The contributor is a female aged 18–29. An image taken at a distance. Reported duration is less than one week. Texture is reported as raised or bumpy. Located on the front of the torso:
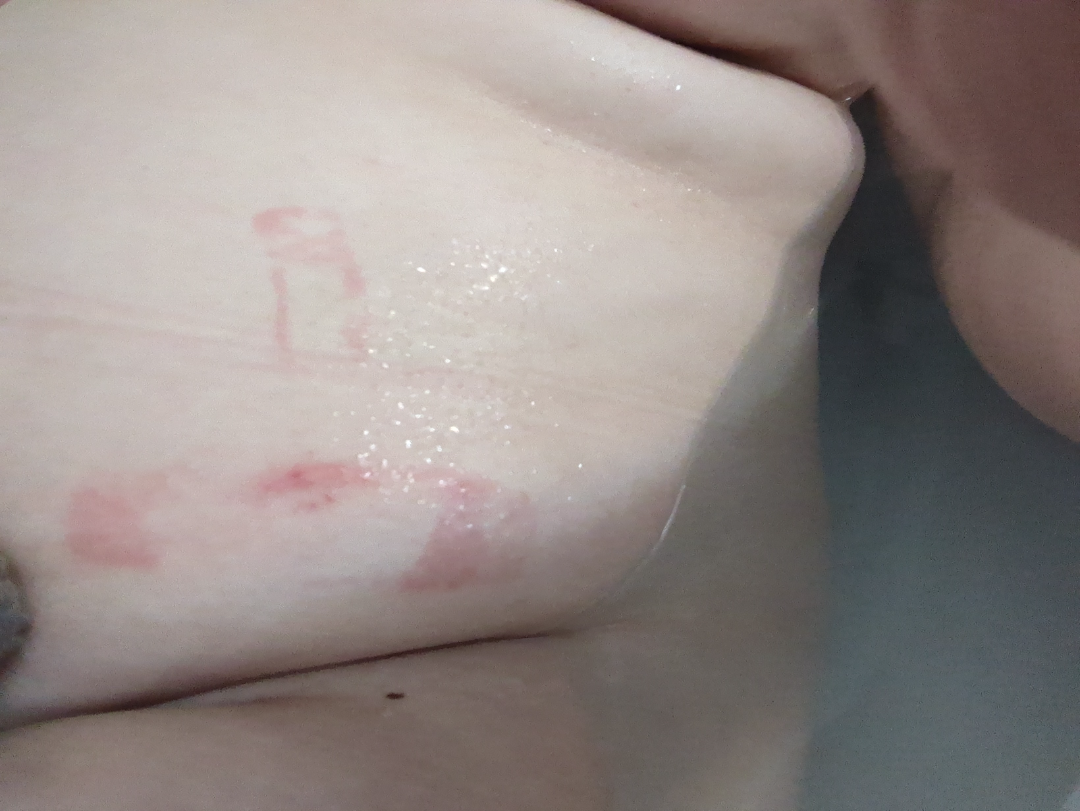Q: What is the dermatologist's impression?
A: the impression is Allergic Contact Dermatitis